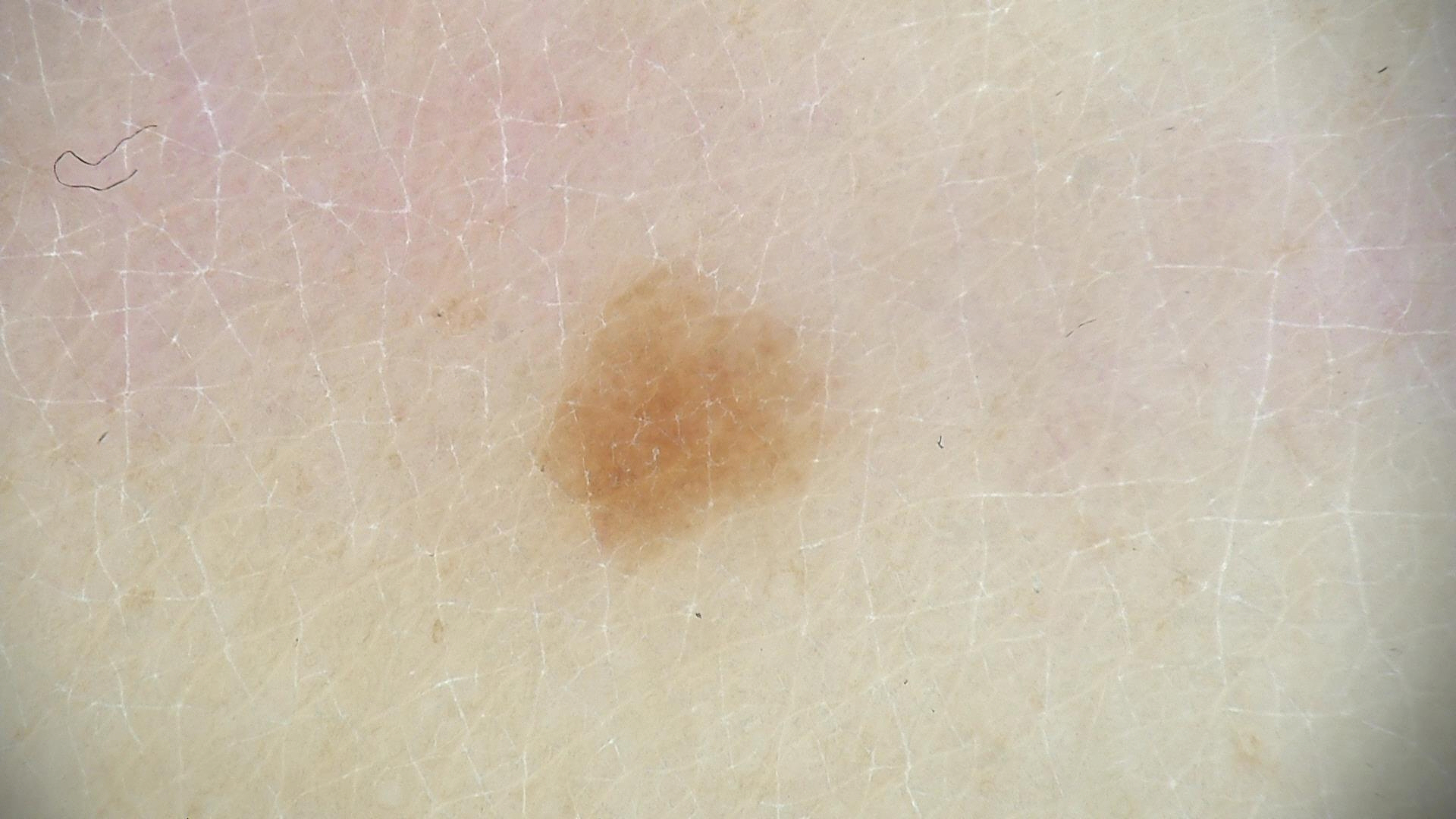Q: What kind of image is this?
A: dermatoscopy
Q: What is the diagnosis?
A: junctional nevus (expert consensus)